The arm is involved. Male contributor, age 18–29. The photograph is a close-up of the affected area:
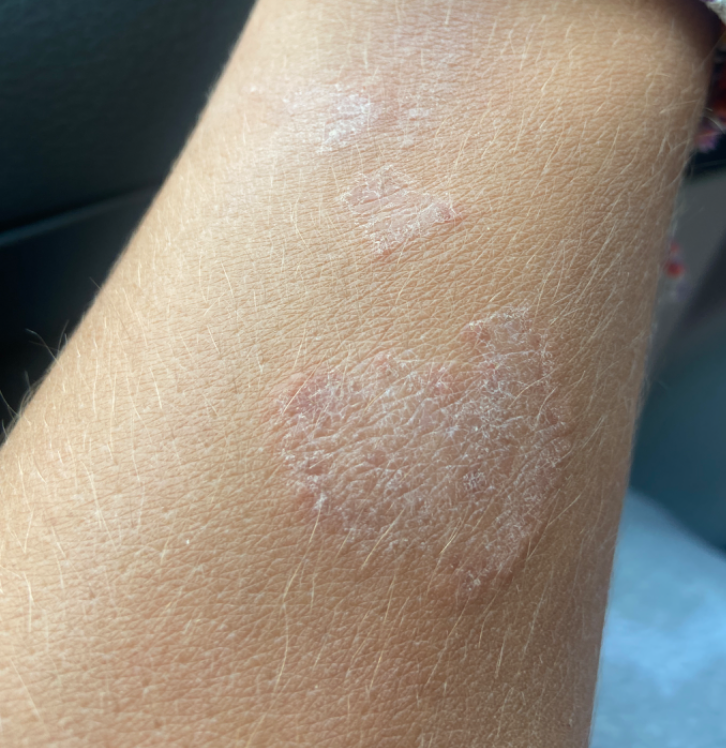Background: The patient notes the lesion is rough or flaky. The patient considered this a rash. Skin tone: Fitzpatrick skin type IV. Findings: On photographic review: the impression was split between Eczema and Psoriasis.